Imaged for a research study, with no referral diagnosis recorded · few moles overall by the patient's own estimate · dermoscopy of a skin lesion · a female subject 60 years old · the patient reports a personal history of skin cancer and a personal history of cancer — 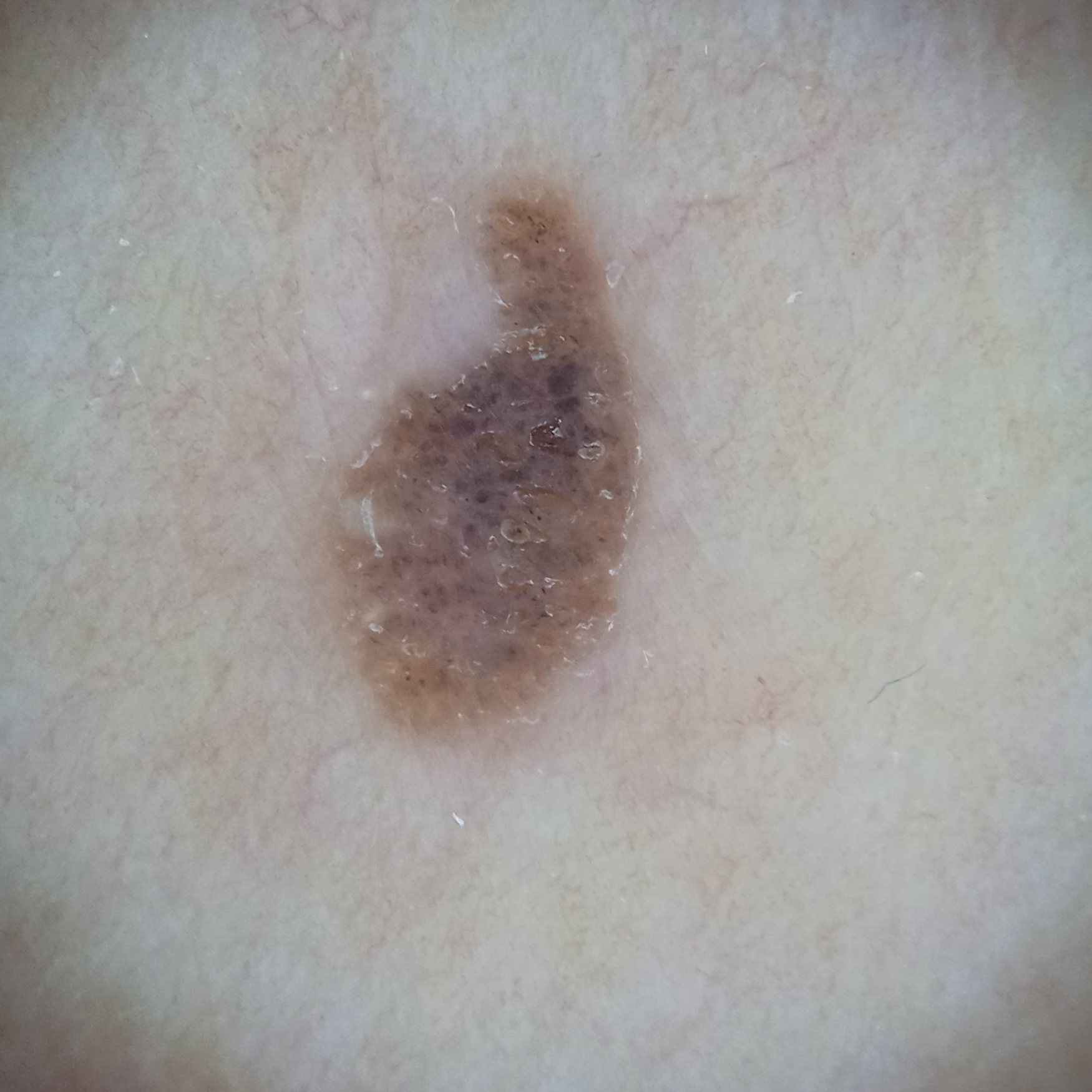The lesion involves the torso. The lesion measures approximately 6.2 mm. The consensus diagnosis for this lesion was a seborrheic keratosis.